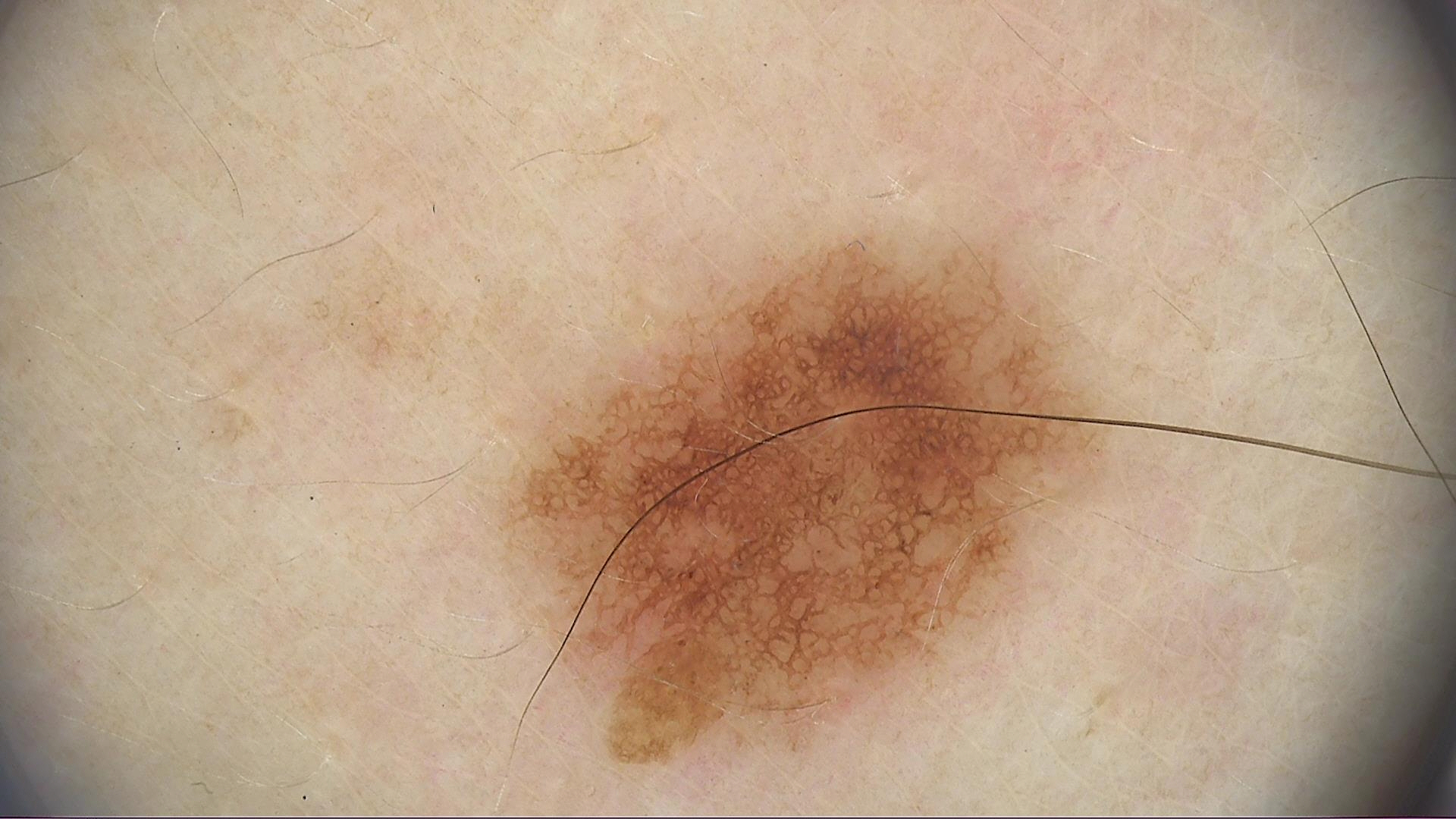Consistent with a benign lesion — a dysplastic junctional nevus.